A skin lesion imaged with a dermatoscope: 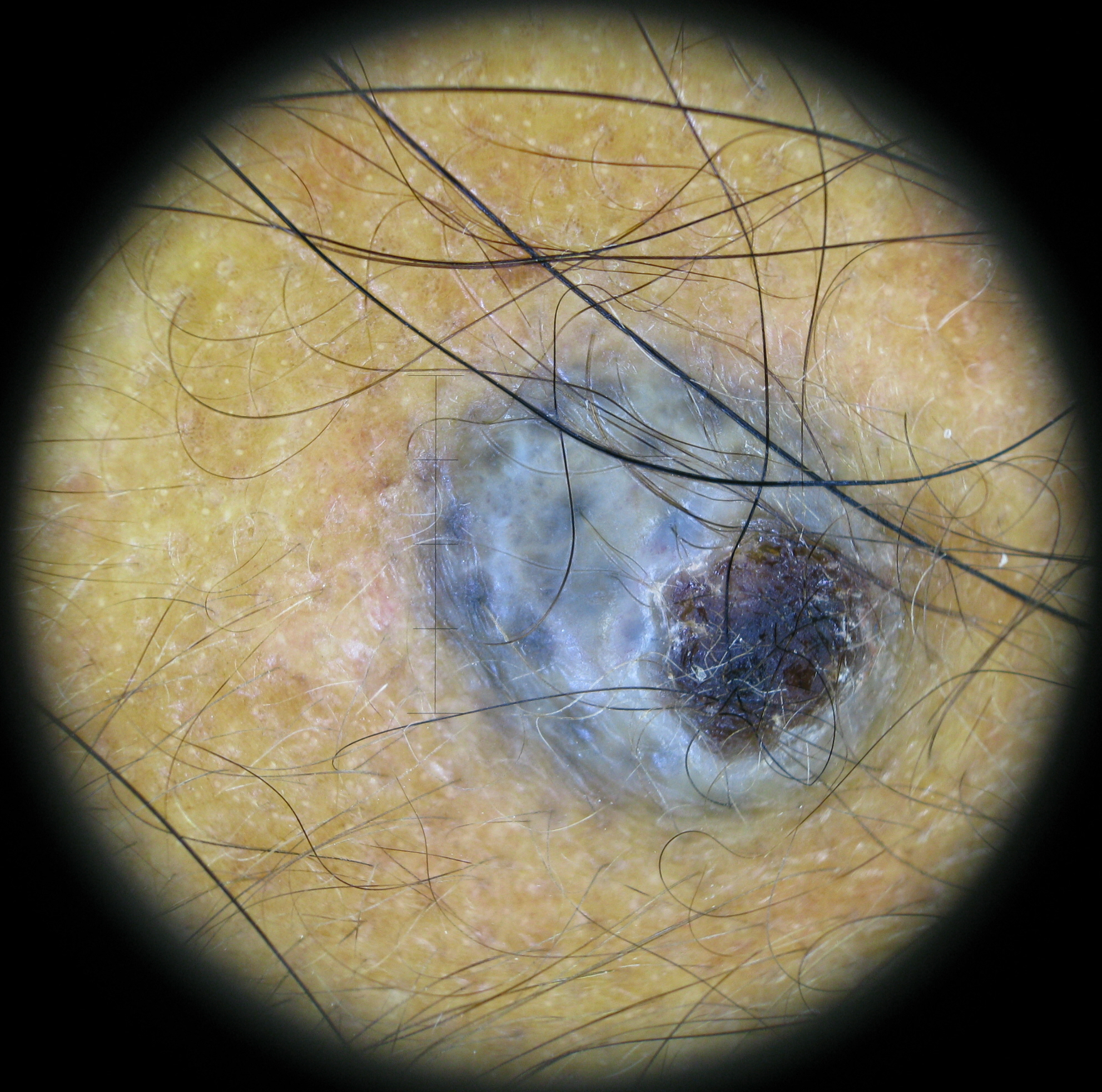The architecture is that of a banal, dermal lesion.
The diagnostic label was a blue nevus.